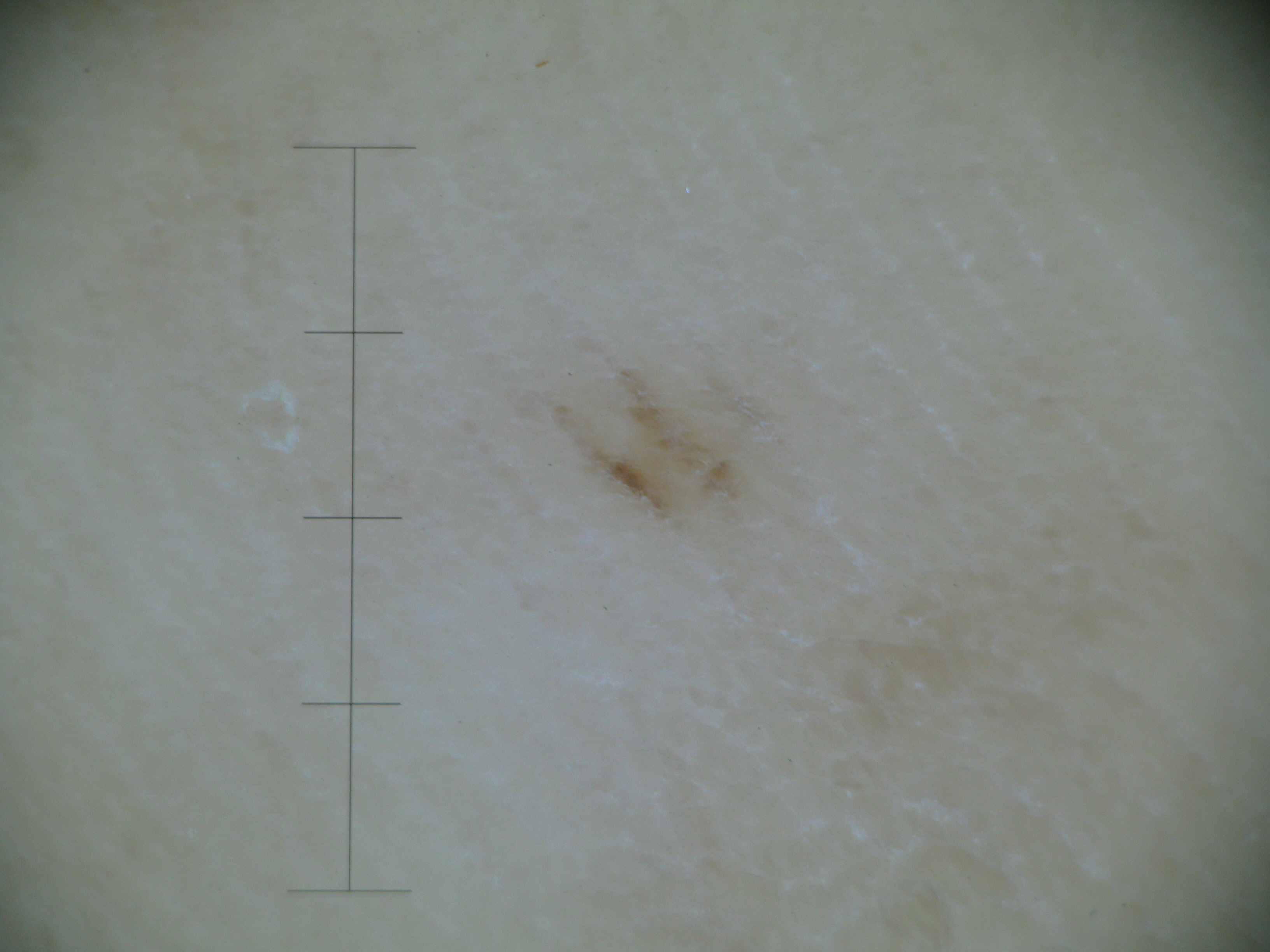Consistent with an acral junctional nevus.